A dermatoscopic image of a skin lesion.
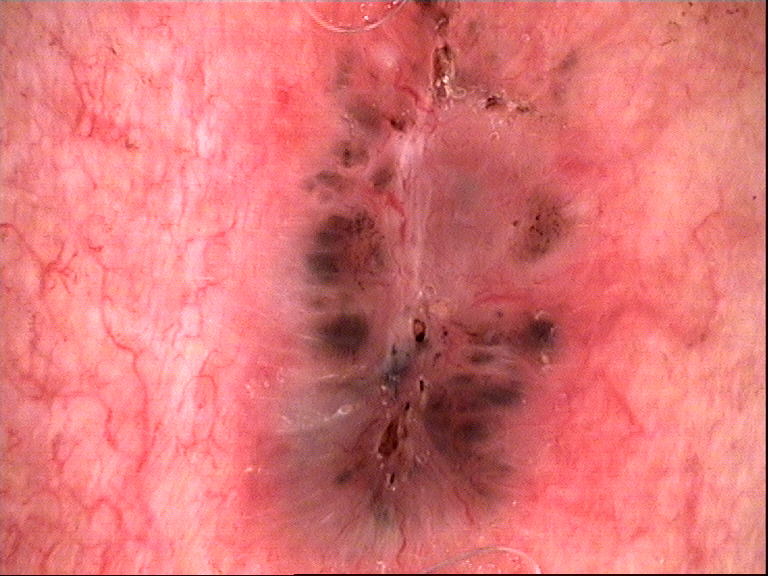Q: How is the lesion classified?
A: keratinocytic
Q: What did the workup show?
A: basal cell carcinoma (biopsy-proven)